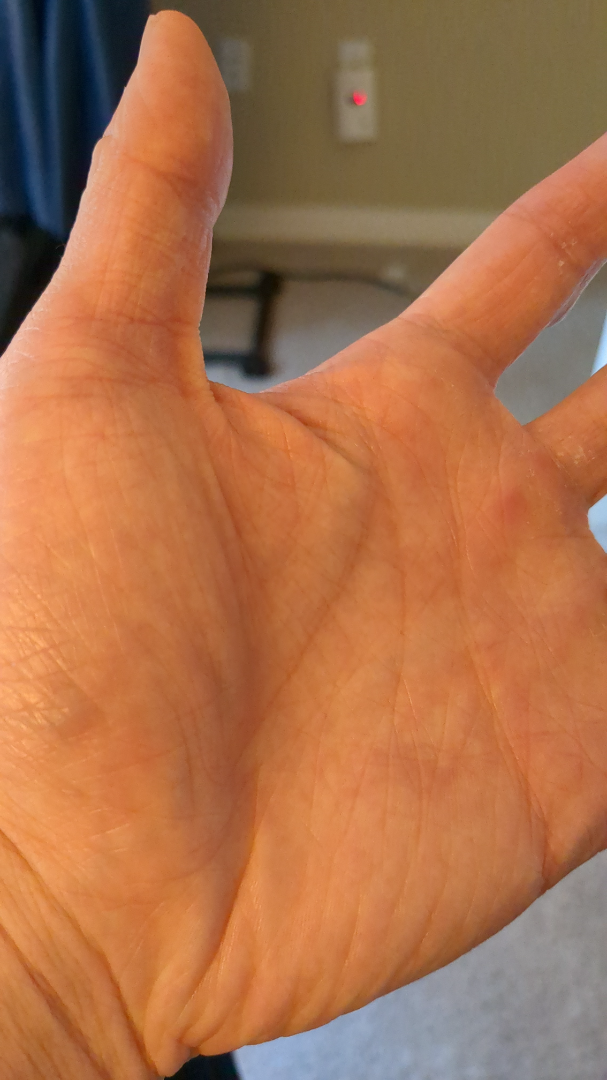  assessment: indeterminate
  shot_type: close-up
  skin_tone:
    monk_skin_tone:
      - 2
      - 4